The lesion involves the leg · an image taken at an angle:
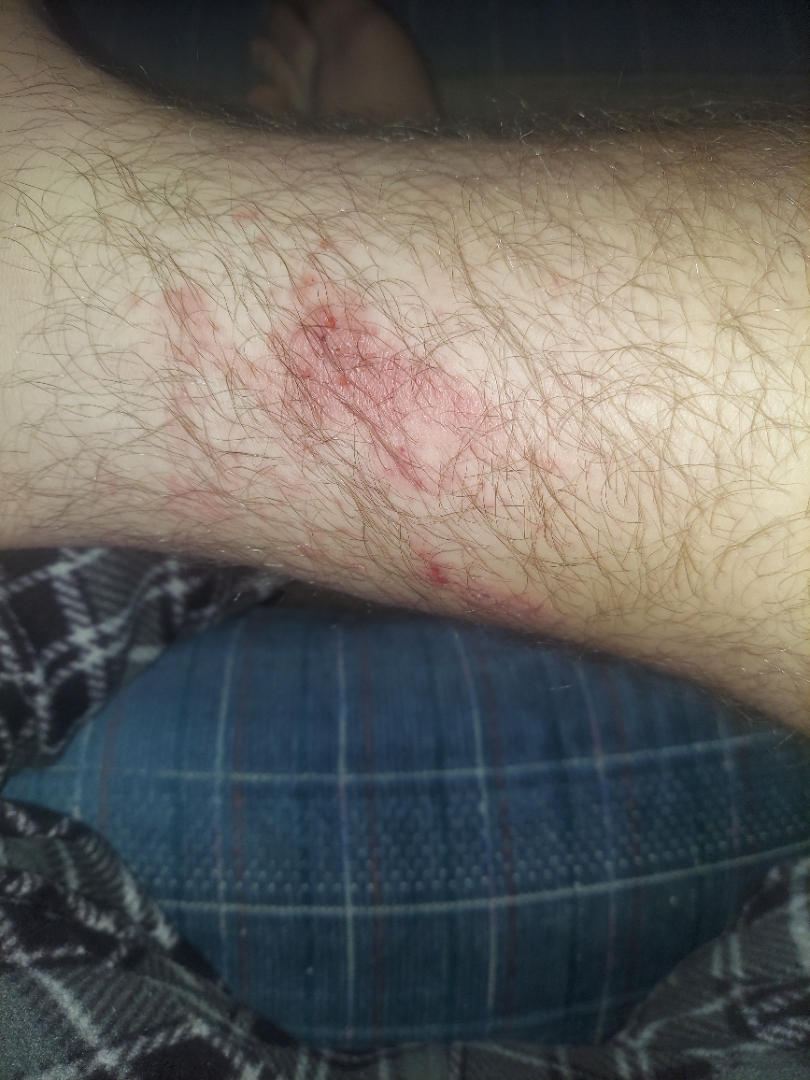assessment — Eczema (0.41); Allergic Contact Dermatitis (0.41); Insect Bite (0.18).